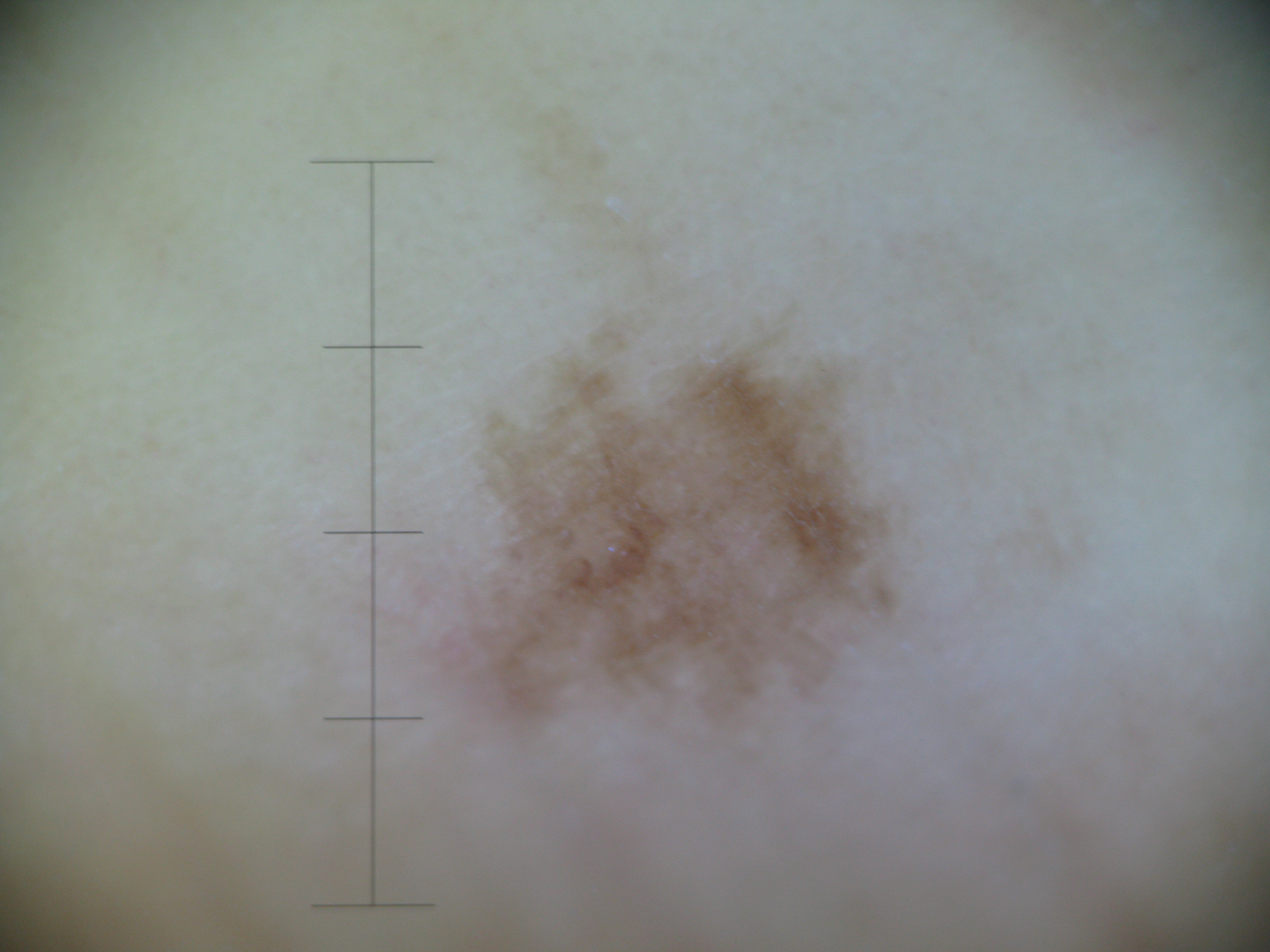Labeled as an acral dysplastic junctional nevus.